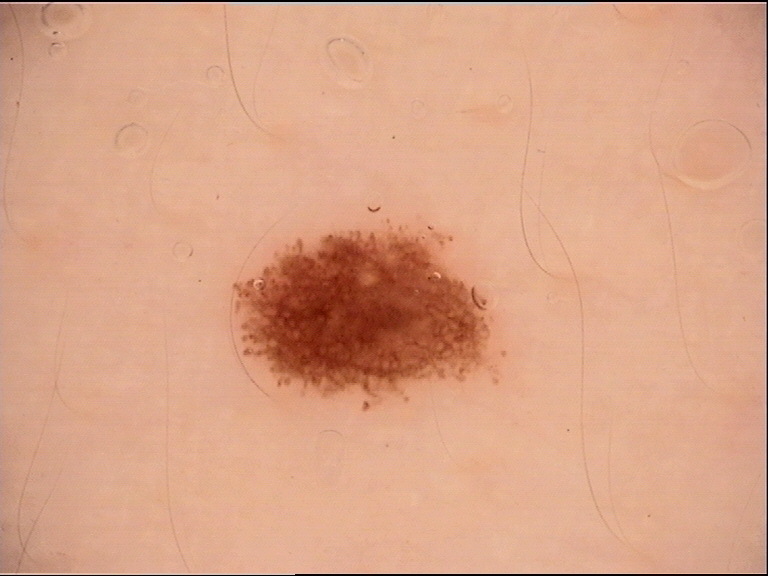{
  "image": "dermatoscopy",
  "diagnosis": {
    "name": "dysplastic junctional nevus",
    "code": "jd",
    "malignancy": "benign",
    "super_class": "melanocytic",
    "confirmation": "expert consensus"
  }
}